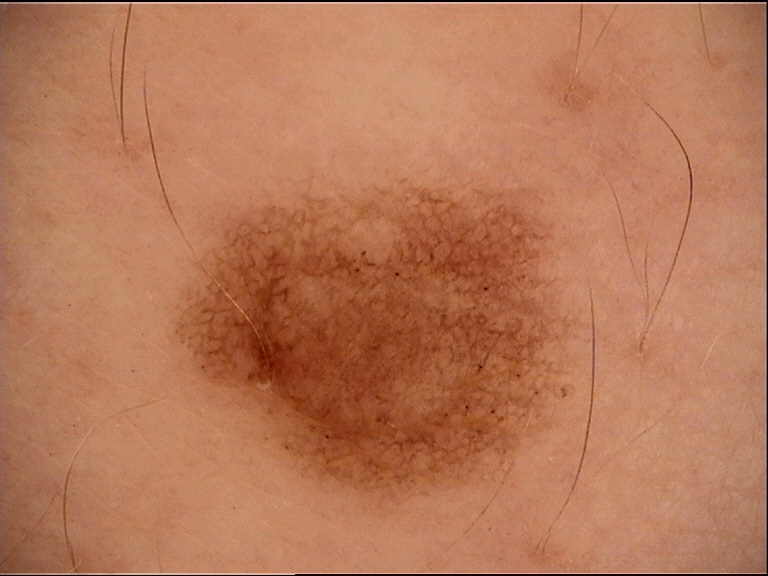Case:
- diagnostic label — dysplastic junctional nevus (expert consensus)